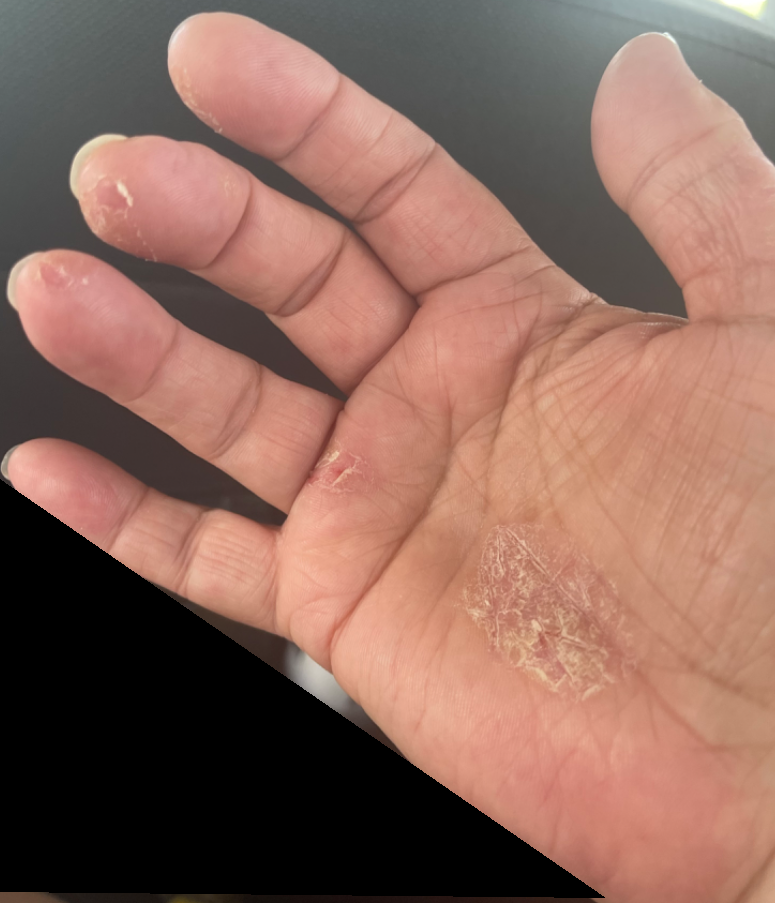Three dermatologists independently reviewed the case: most consistent with Psoriasis; also consider Eczema; less likely is Tinea.